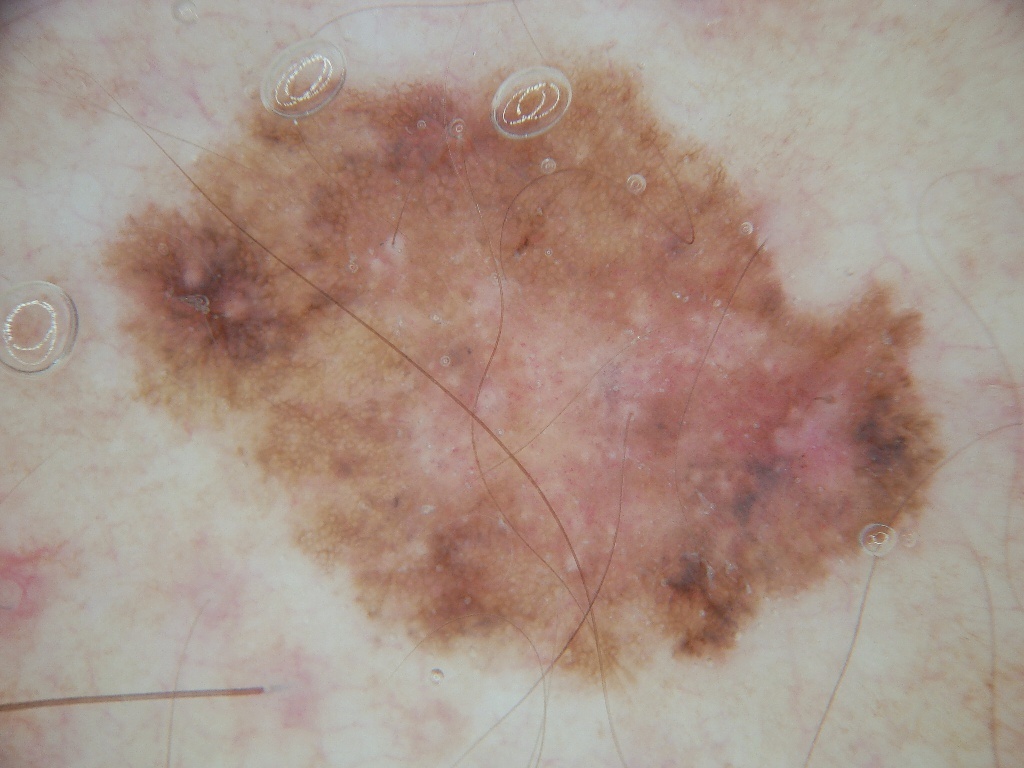Image and clinical context:
This is a dermoscopic photograph of a skin lesion. The lesion occupies roughly 44% of the field. The lesion is located at <box>99, 64, 948, 684</box>.
Assessment:
Expert review diagnosed this as a benign skin lesion.